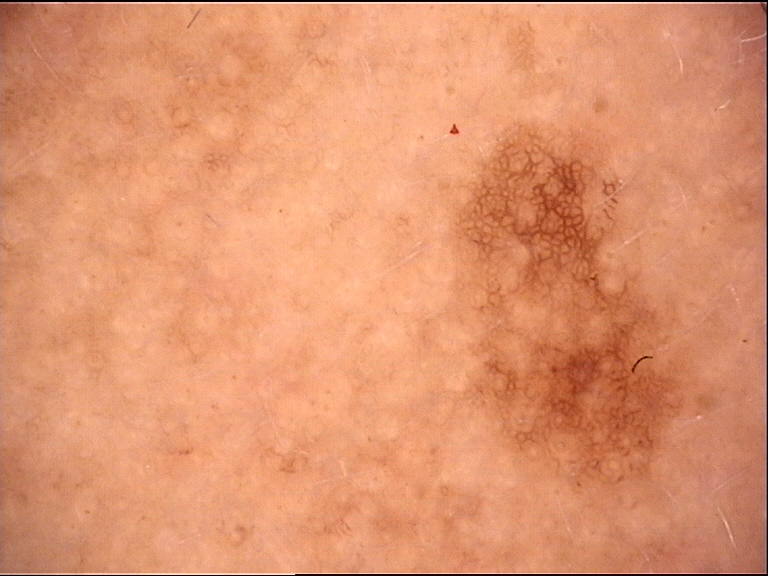{"image": "dermoscopy", "diagnosis": {"name": "dysplastic junctional nevus", "code": "jd", "malignancy": "benign", "super_class": "melanocytic", "confirmation": "expert consensus"}}